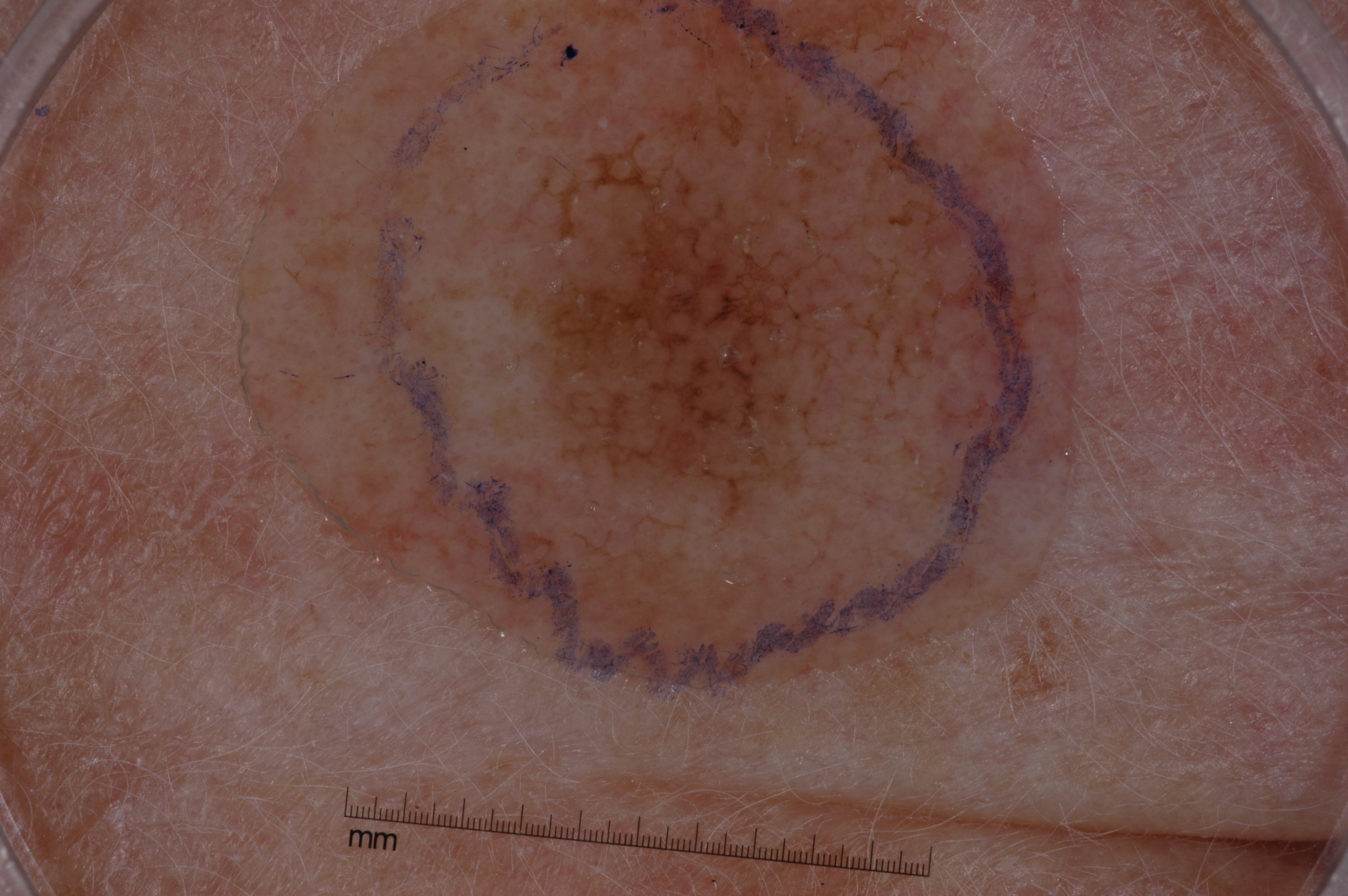Case summary:
• patient: female, aged 68 to 72
• modality: dermoscopy of a skin lesion
• size: large
• lesion margin: clipped at the frame edge
• lesion bbox: (327, 0, 1085, 679)
• dermoscopic features assessed but absent: streaks, pigment network, milia-like cysts, and negative network
• diagnosis: a melanoma